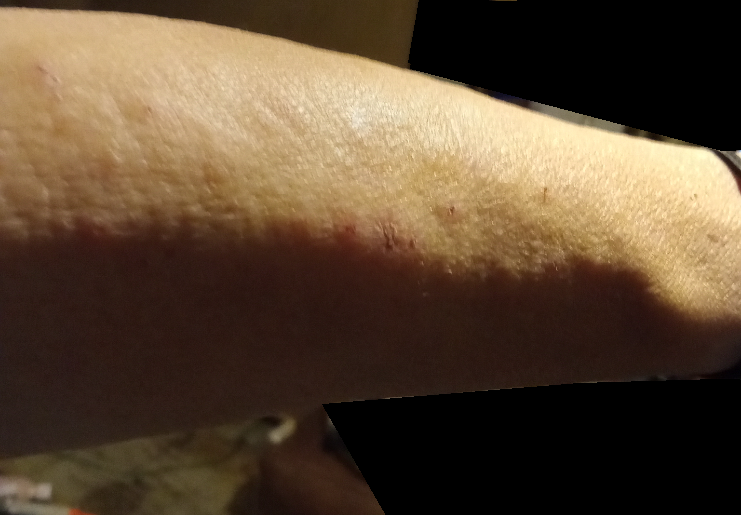The photograph was taken at an angle.
The contributor is a female aged 50–59.
The reviewing dermatologist's impression was: Eczema (leading).